Close-up view, the arm is involved — 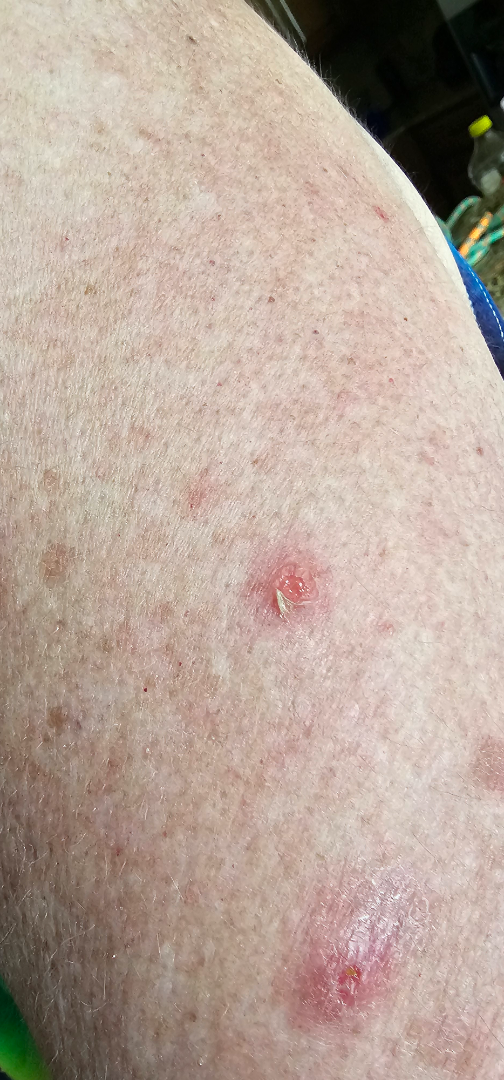| key | value |
|---|---|
| lesion texture | fluid-filled |
| assessment | Eczema (possible); Insect Bite (possible); Inflicted skin lesions (possible) |